A moderate number of moles by the patient's own estimate · the patient says their skin reddens painfully with sun exposure · a female subject age 55 · acquired for a research image collection, with no referral diagnosis · dermoscopy of a skin lesion · the patient reports immunosuppression, a prior organ transplant, no sunbed use, and no personal history of skin cancer.
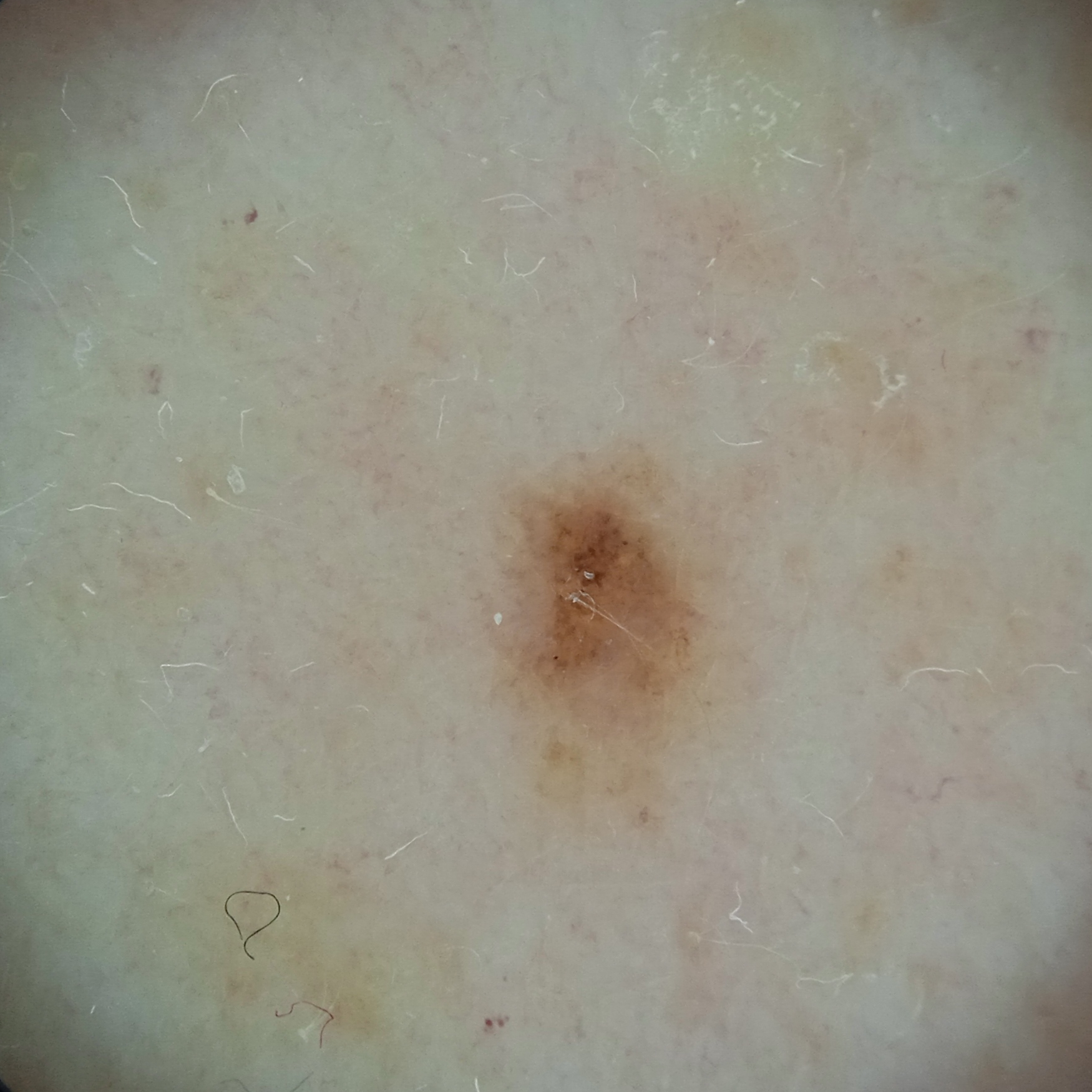The lesion is about 2.5 mm across.
Dermatologist review favored a melanocytic nevus.